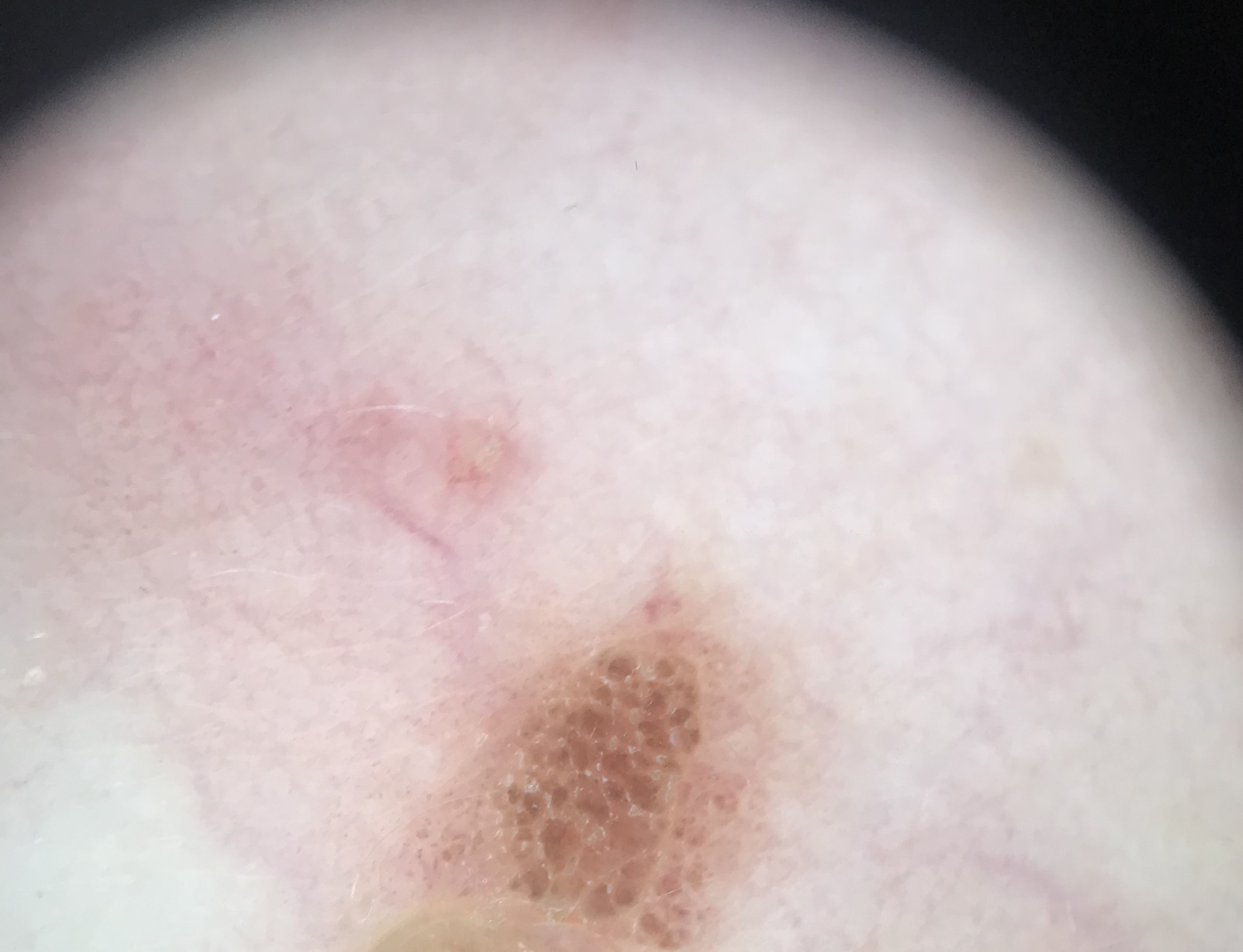A dermoscopy image of a single skin lesion.
The architecture is that of a keratinocytic lesion.
Consistent with a benign lesion — a seborrheic keratosis.